Texture is reported as raised or bumpy. The affected area is the leg and top or side of the foot. Reported duration is about one day. The photograph was taken at a distance:
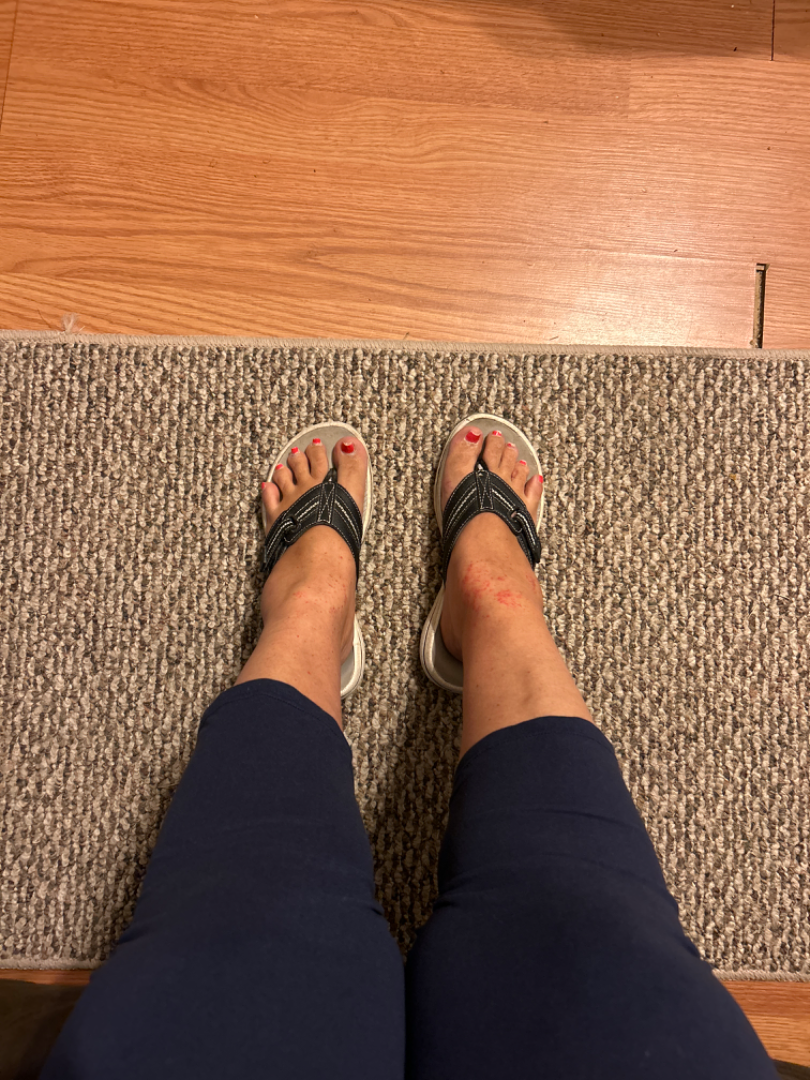Pigmented purpuric eruption (most likely); Purpura (possible); Vasculitis of the skin (possible).